A dermoscopic close-up of a skin lesion. The subject is a female roughly 65 years of age: 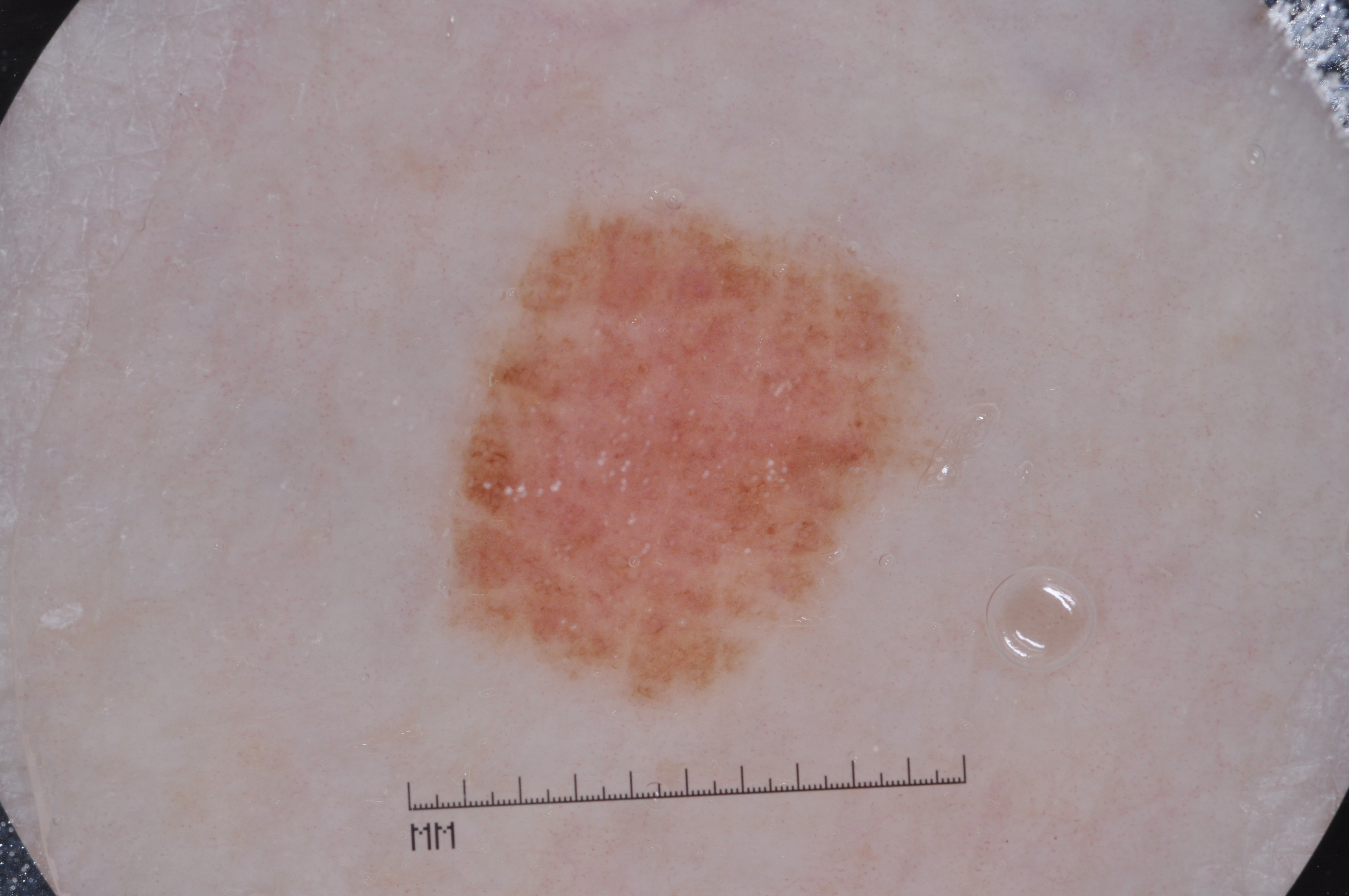Findings:
The lesion takes up about 14% of the image. The visible lesion spans left=443, top=210, right=927, bottom=700. Dermoscopic review identifies pigment network and milia-like cysts, with no streaks or negative network.
Impression:
The lesion was assessed as a melanocytic nevus.